A dermoscopy image of a single skin lesion.
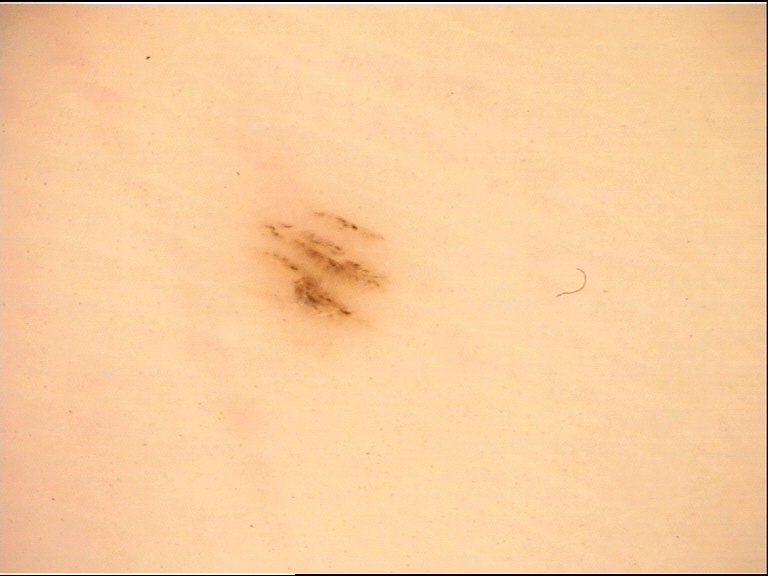The diagnostic label was a banal lesion — an acral junctional nevus.